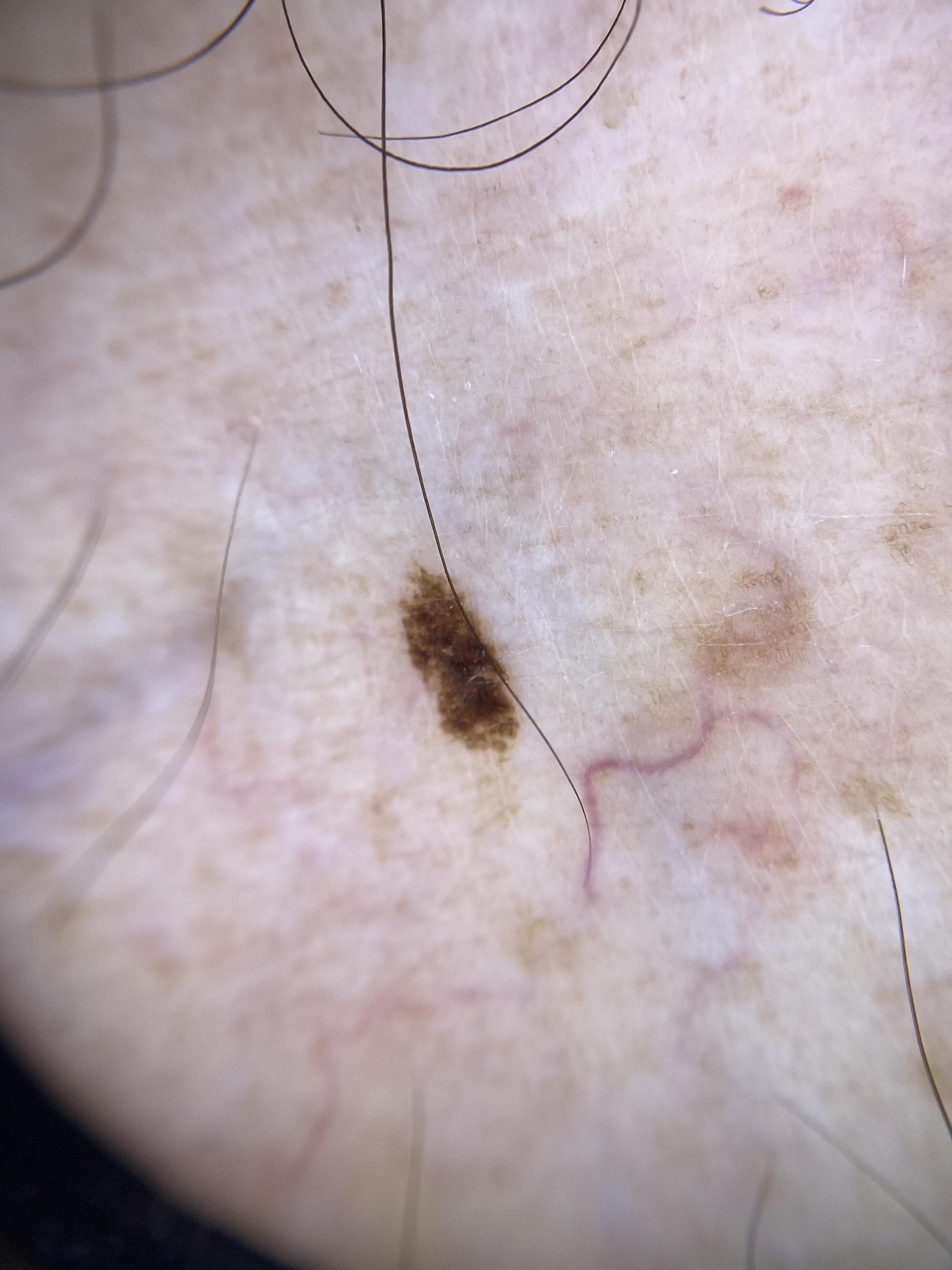image=dermoscopy | subject=male, approximately 85 years of age or older | assessment=Nevus.